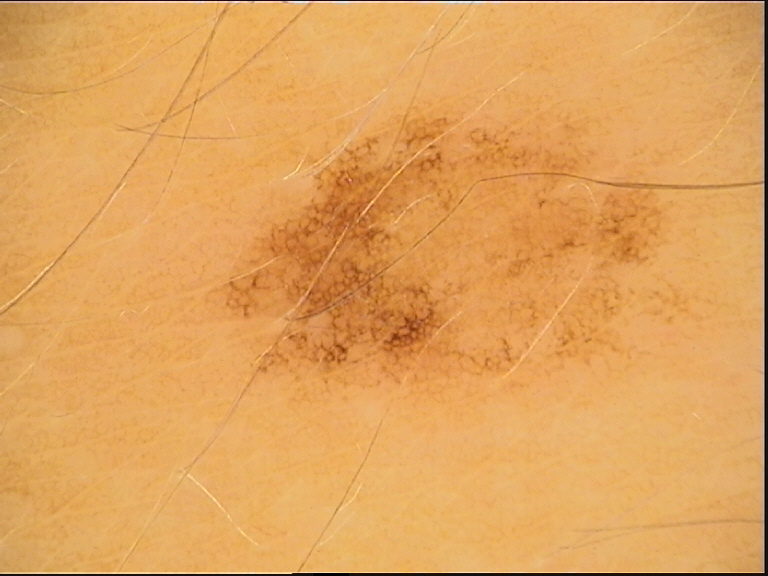Q: What kind of image is this?
A: dermoscopy
Q: What is the diagnosis?
A: dysplastic junctional nevus (expert consensus)